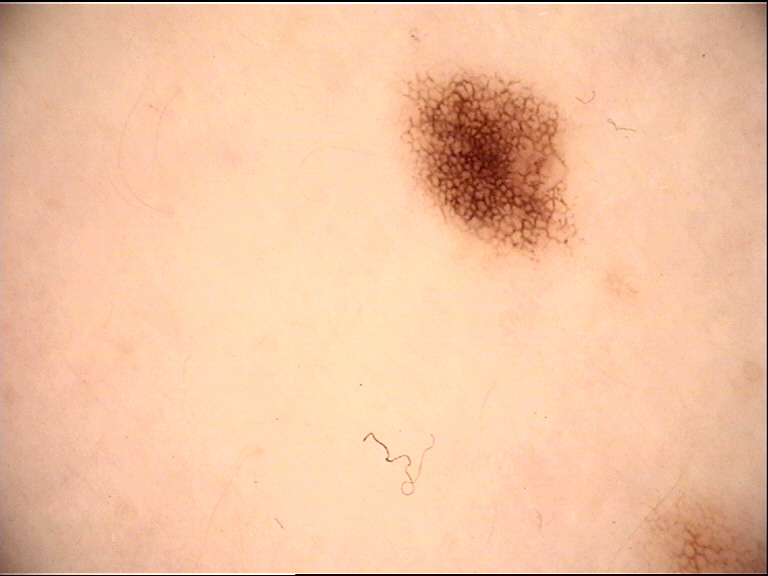Labeled as a junctional nevus.